Dermoscopy of a skin lesion:
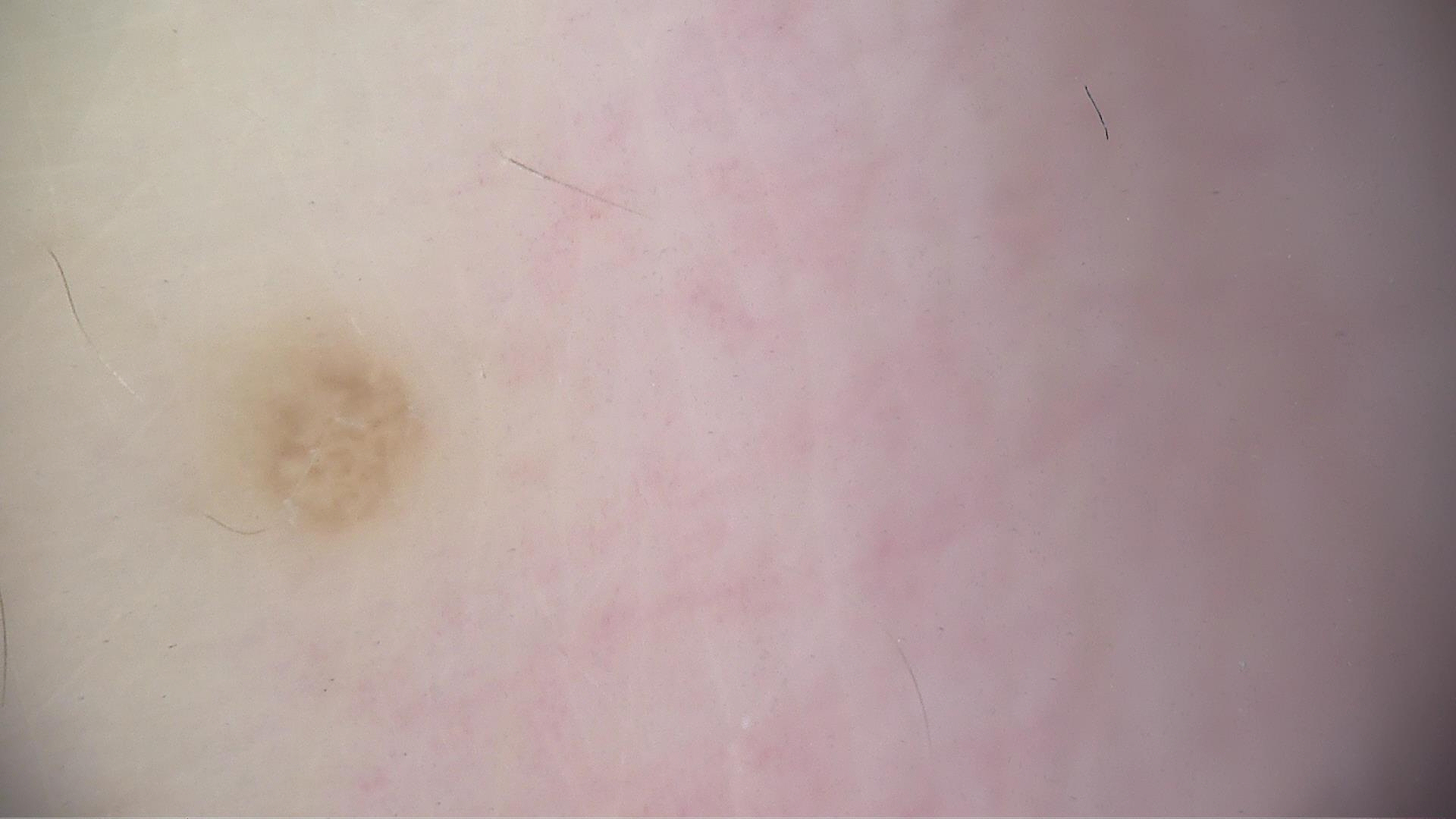The architecture is that of a banal lesion. Labeled as a dermal nevus.